Located on the leg, an image taken at a distance, the contributor is a male aged 18–29 — 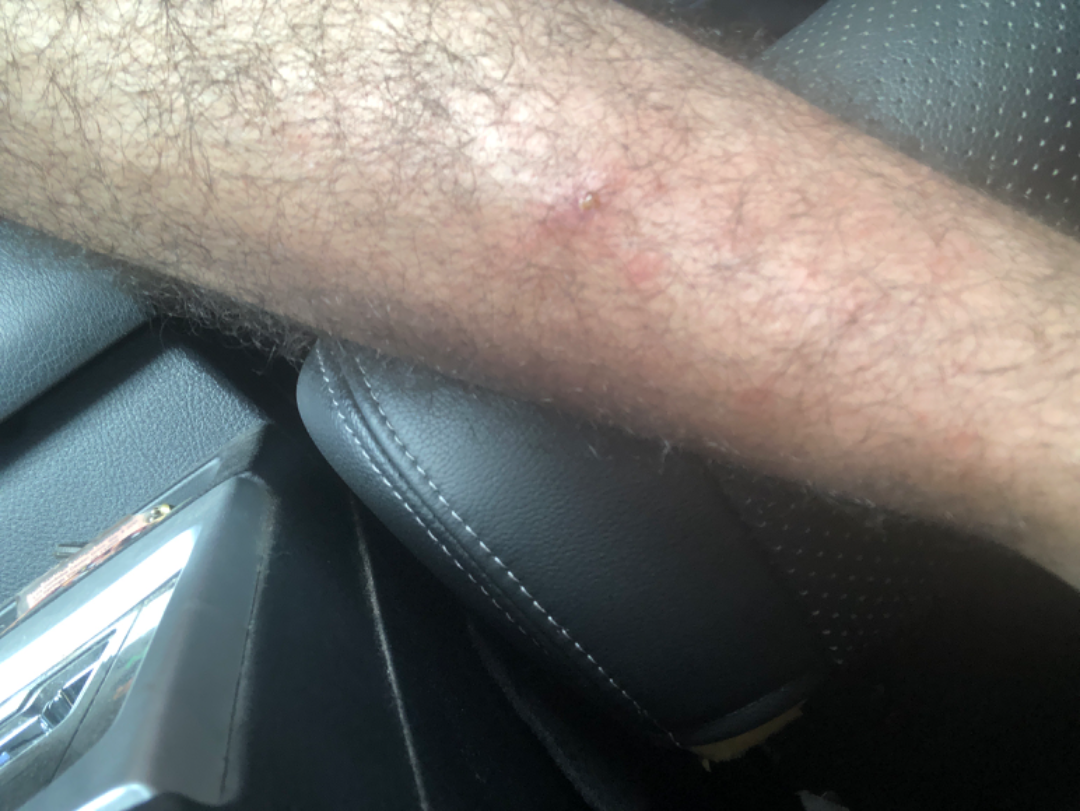{
  "differential": {
    "tied_lead": [
      "Impetigo",
      "Cellulitis",
      "Eczema"
    ]
  }
}